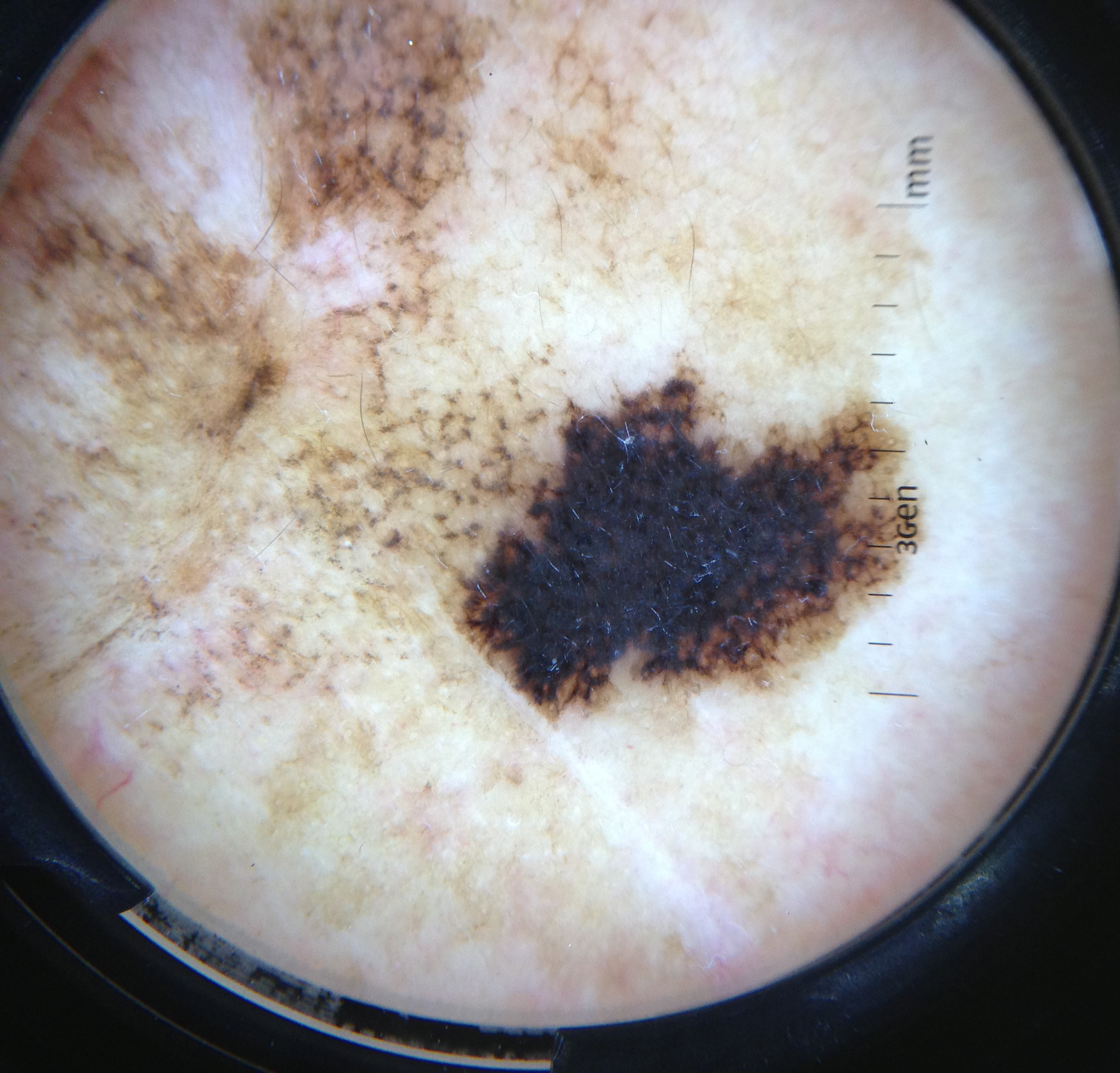- pathology: lentigo maligna (biopsy-proven)